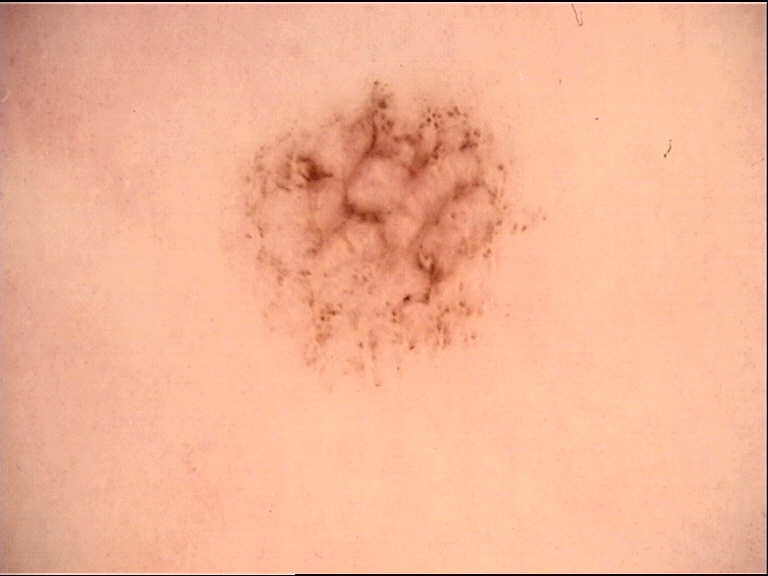– class: acral dysplastic junctional nevus (expert consensus)